A dermoscopic close-up of a skin lesion:
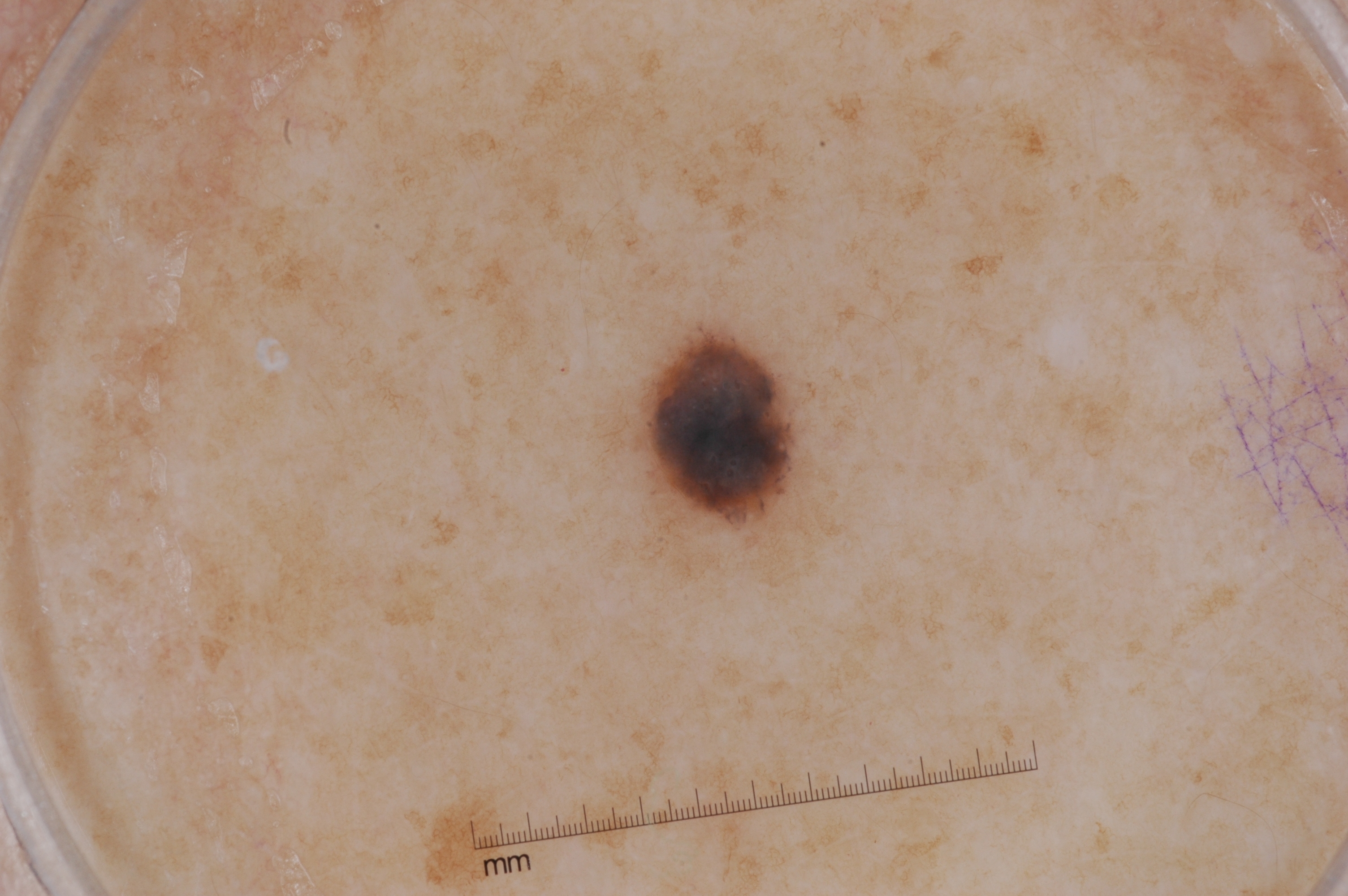Findings:
• dermoscopic features: pigment network and milia-like cysts
• size: small
• location: bbox(633, 321, 804, 531)
• impression: a melanocytic nevus, a benign skin lesion